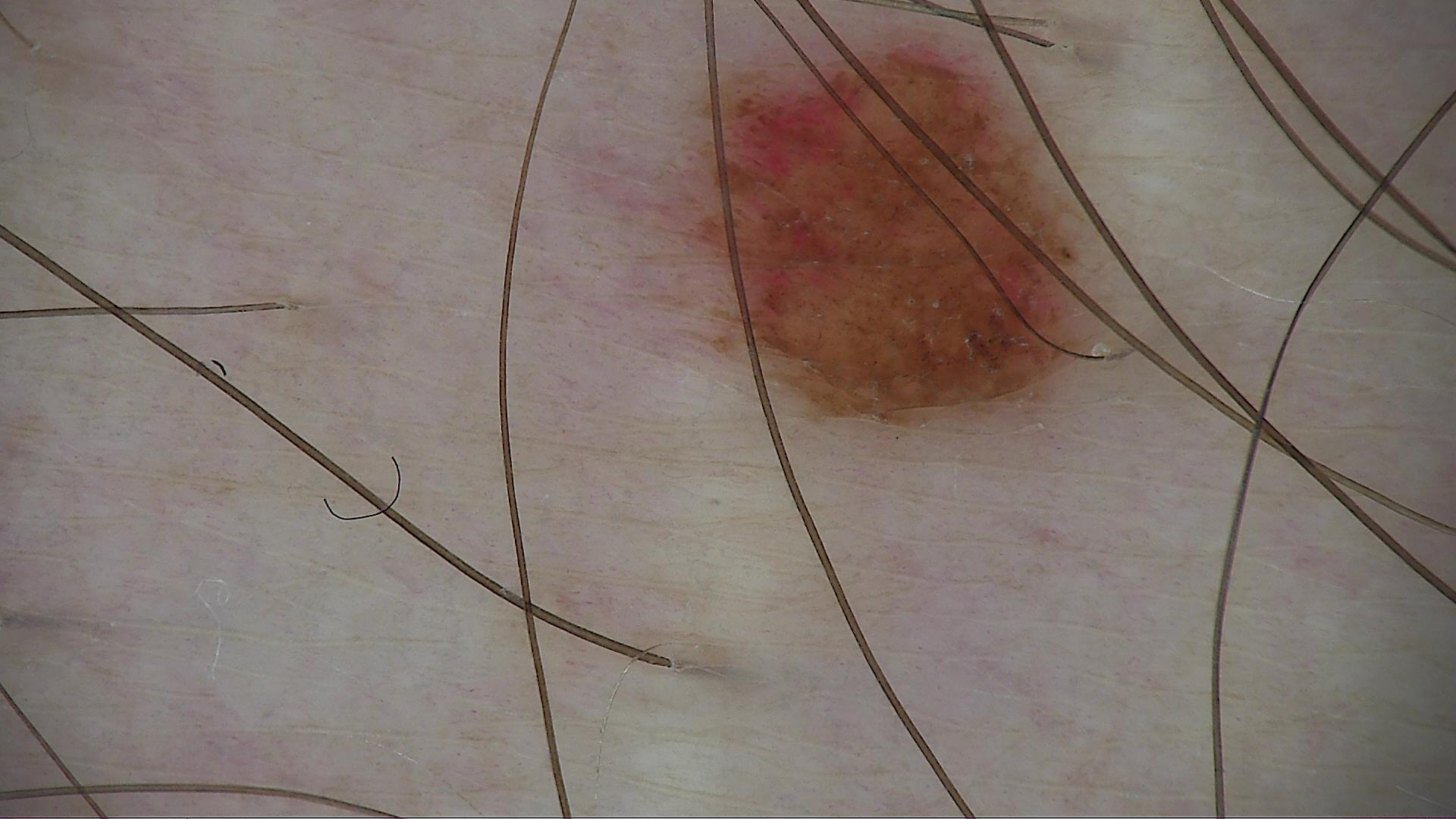image type — dermoscopy | subtype — banal | diagnosis — compound nevus (expert consensus).